The patient considered this a rash; a close-up photograph; reported duration is less than one week; the lesion is described as raised or bumpy; symptoms reported: burning, itching and pain; the lesion involves the leg; the patient is a female aged 40–49.
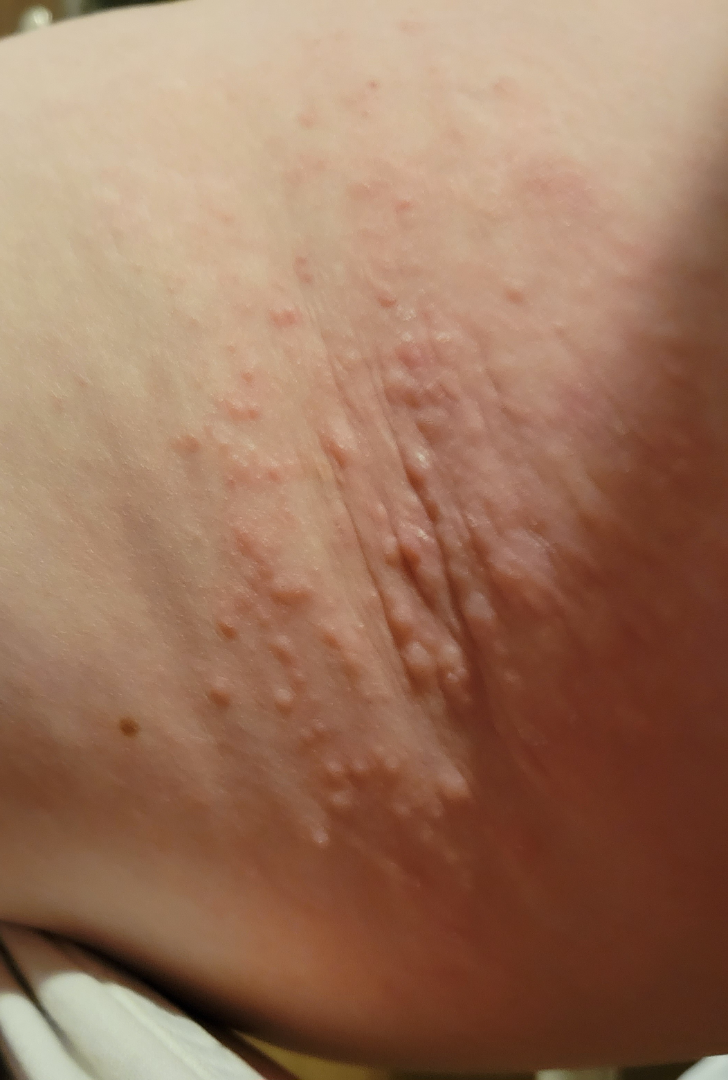No differential diagnosis could be assigned on photographic review.